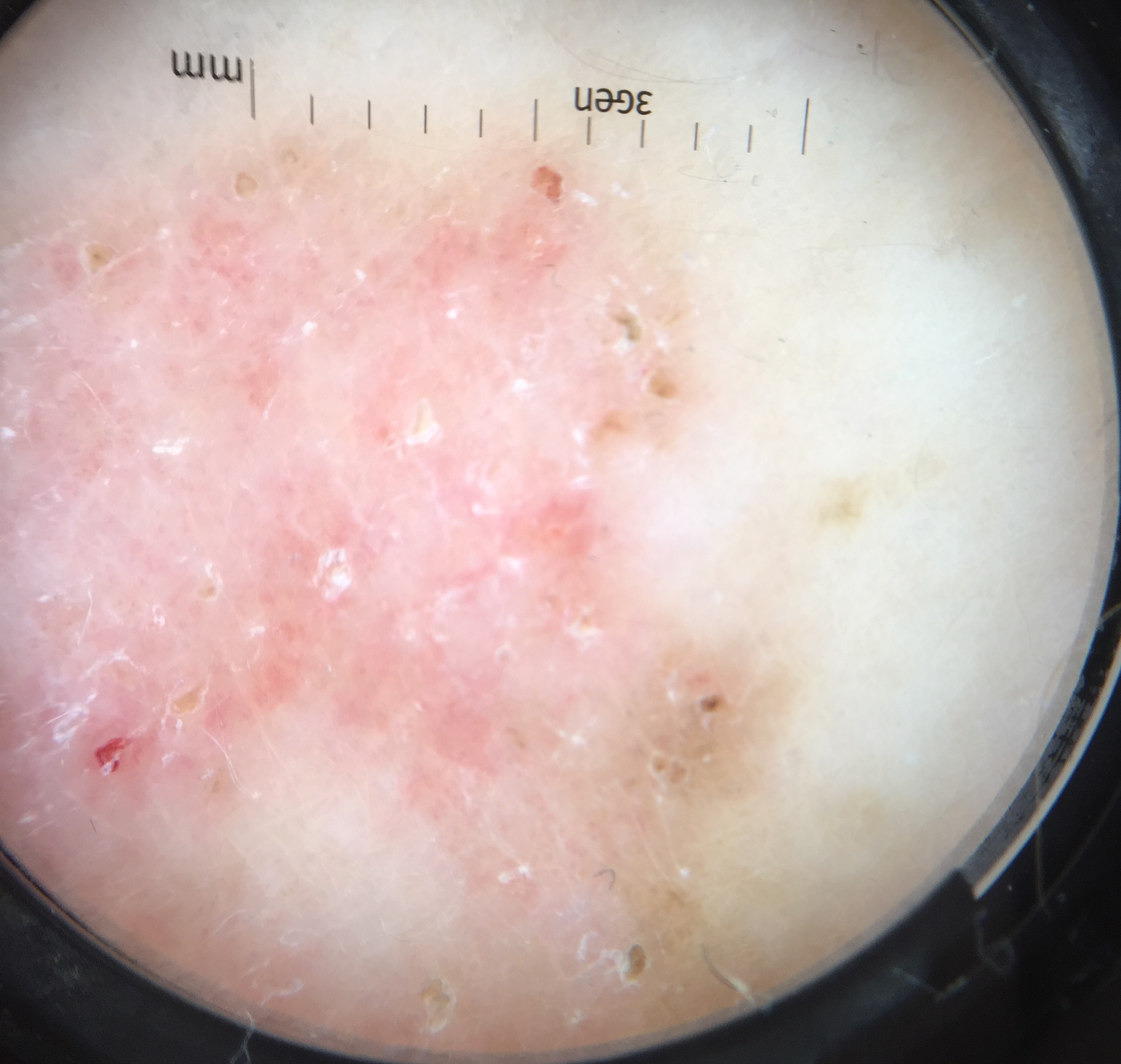Pathology: The biopsy diagnosis was a keratinocytic lesion — a basal cell carcinoma.